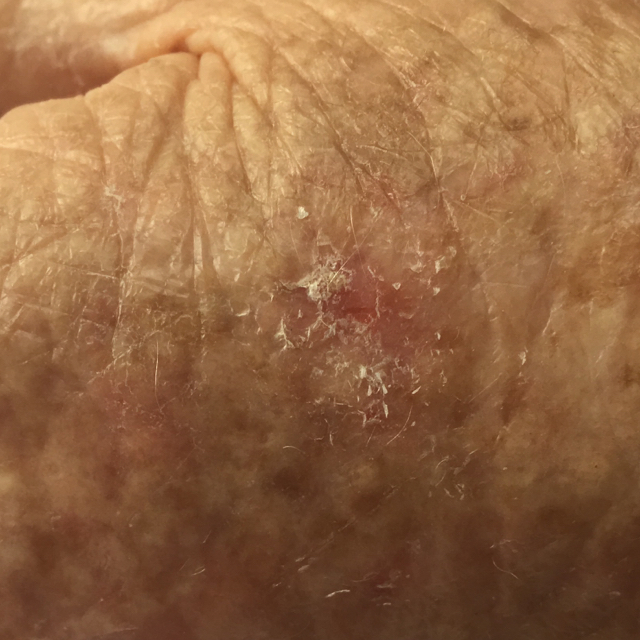The diagnostic impression was an actinic keratosis.